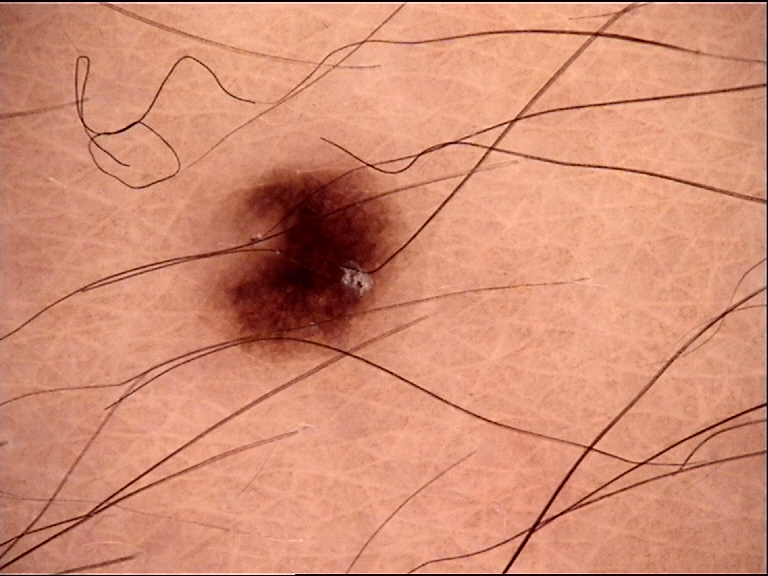Consistent with a junctional nevus.